Close-up view. The subject is 50–59, male. The leg is involved:
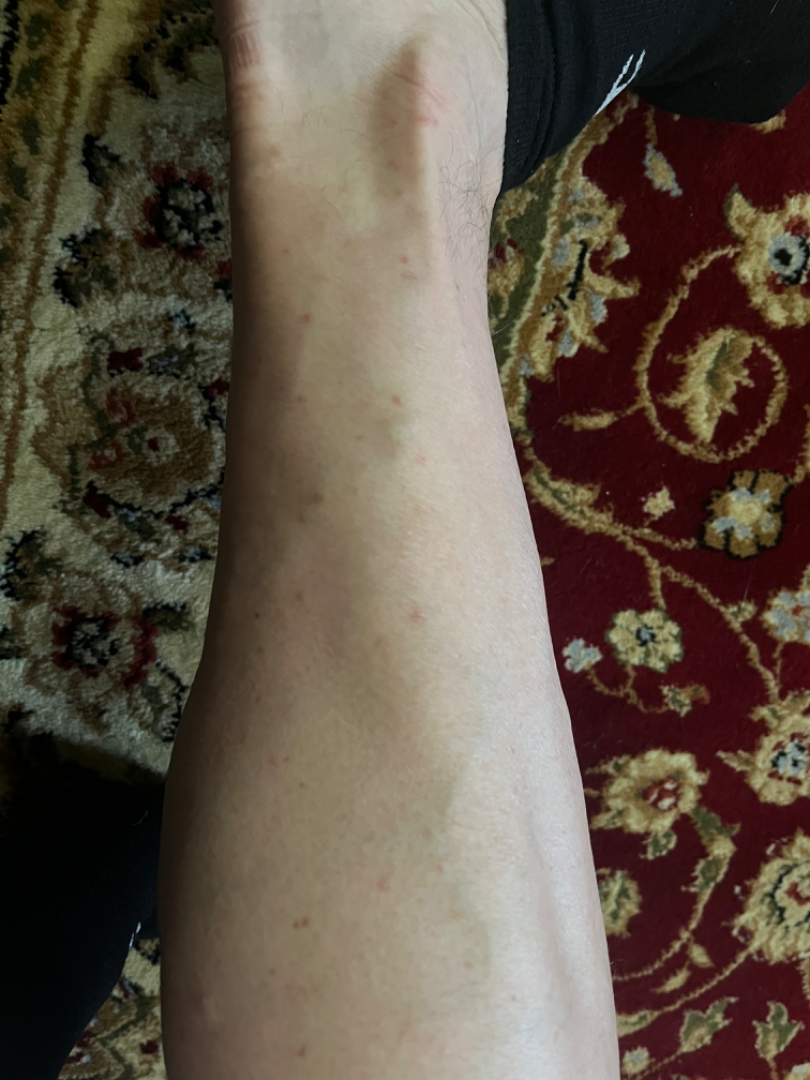<dermatology_case>
  <assessment>no clear pathology</assessment>
  <duration>one to four weeks</duration>
  <texture>raised or bumpy</texture>
  <symptoms>bothersome appearance</symptoms>
  <patient_category>a rash</patient_category>
  <systemic_symptoms>none reported</systemic_symptoms>
</dermatology_case>